A clinical photo of a skin lesion taken with a smartphone · a male patient in their 70s.
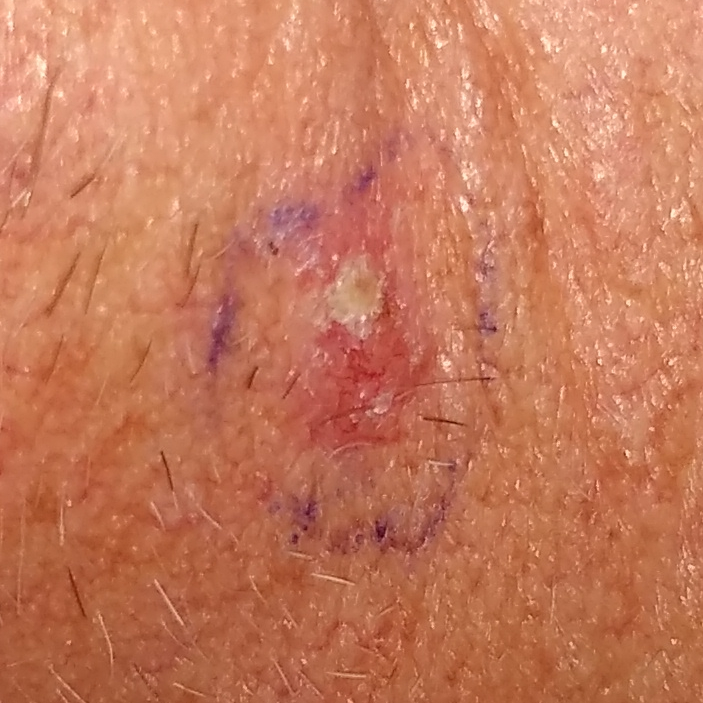| field | value |
|---|---|
| location | an ear |
| diagnostic label | basal cell carcinoma (biopsy-proven) |